The patient is a male aged around 55; a dermoscopy image of a single skin lesion.
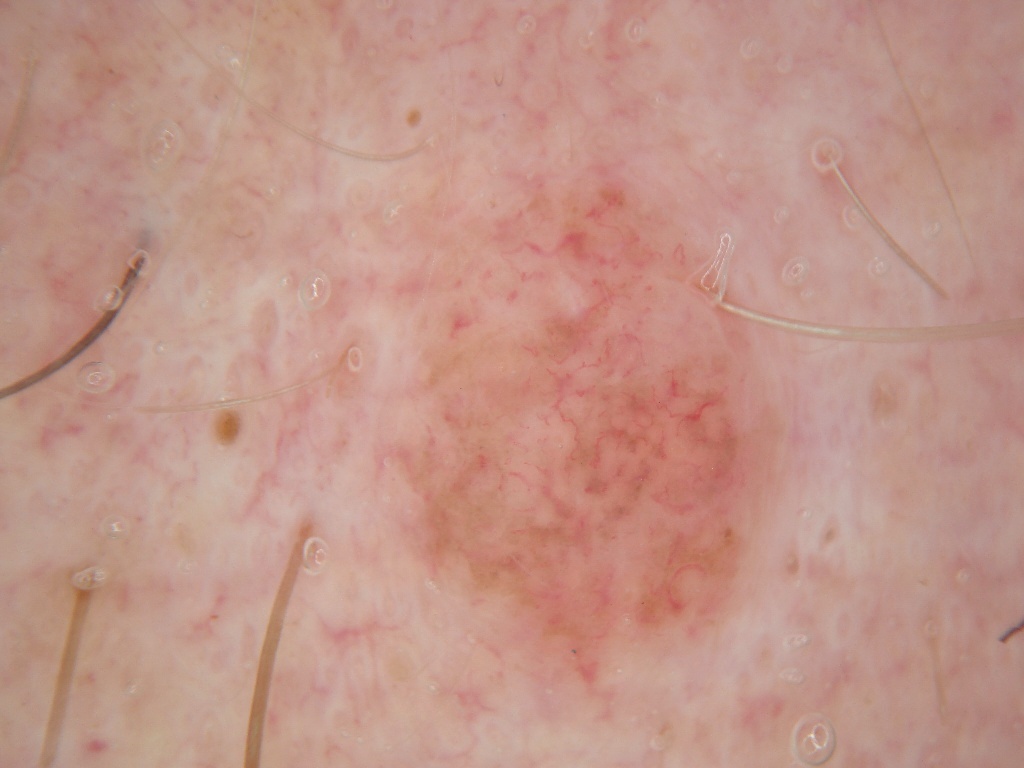Summary:
A moderately sized lesion. Dermoscopically, the lesion shows no globules, streaks, negative network, pigment network, or milia-like cysts. In (x1, y1, x2, y2) order, the lesion is bounded by 358/153/787/703.
Impression:
Consistent with a melanocytic nevus.